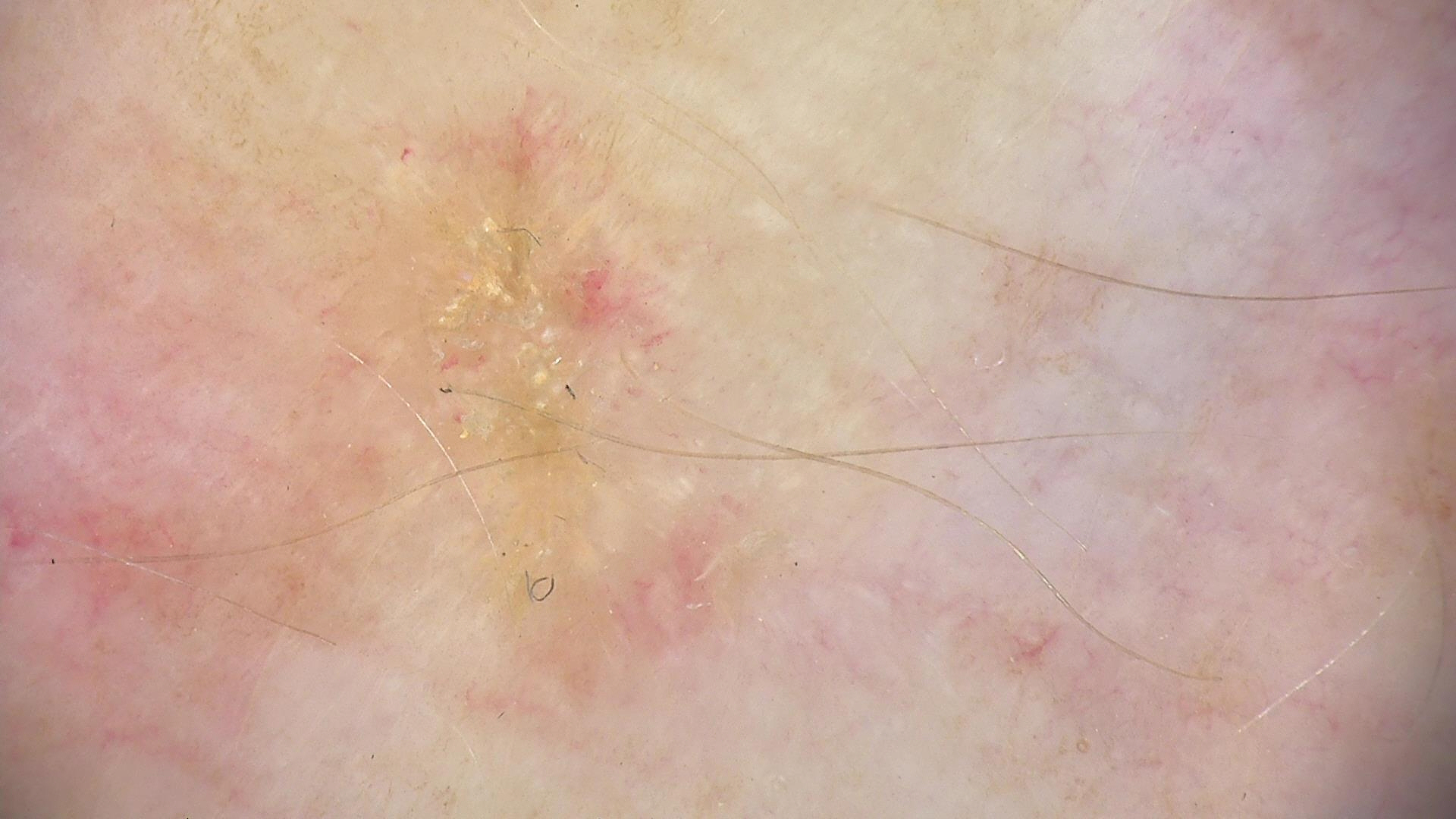Findings:
– modality — dermatoscopy
– class — actinic keratosis (expert consensus)